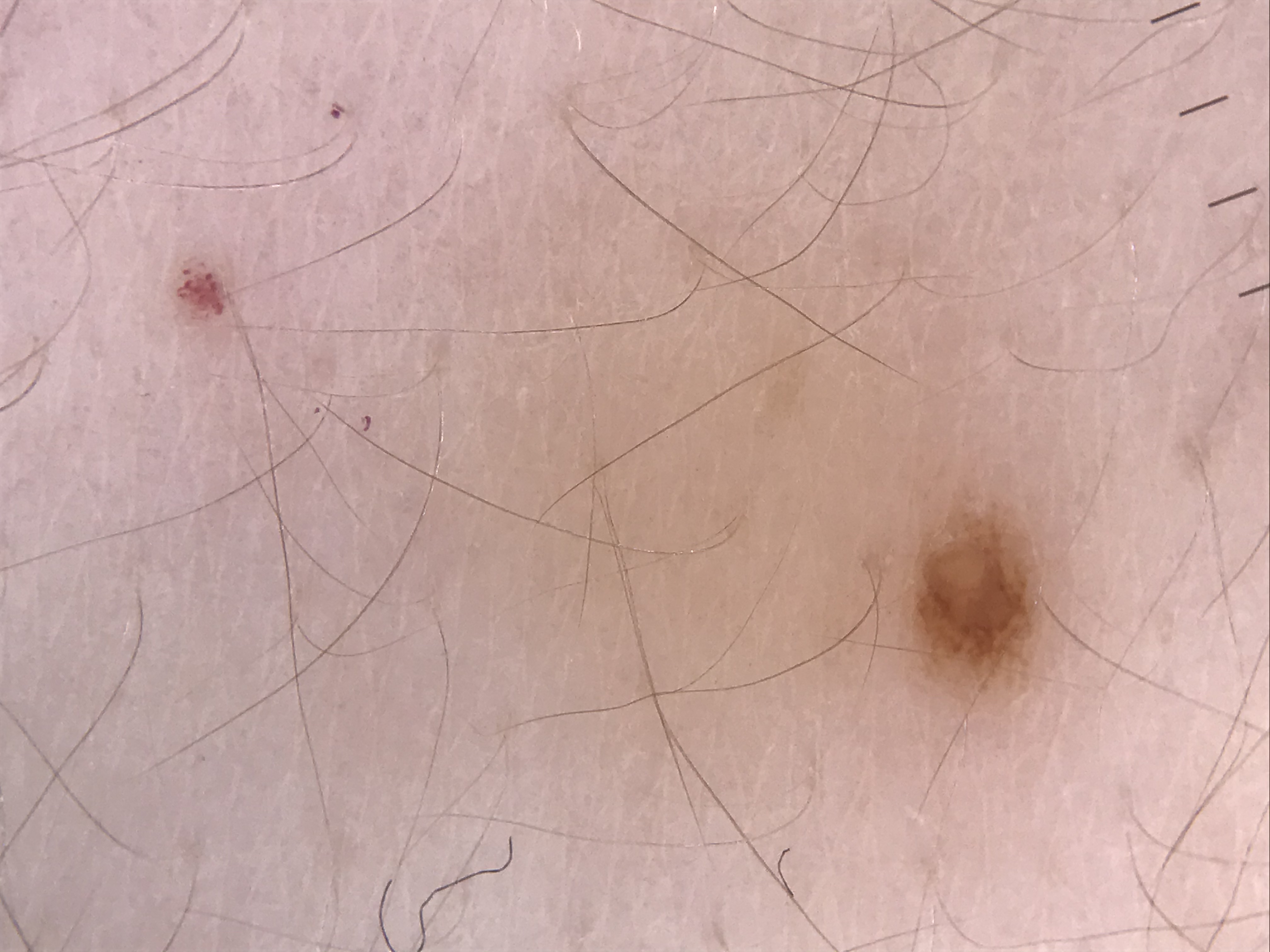class=junctional nevus (expert consensus).